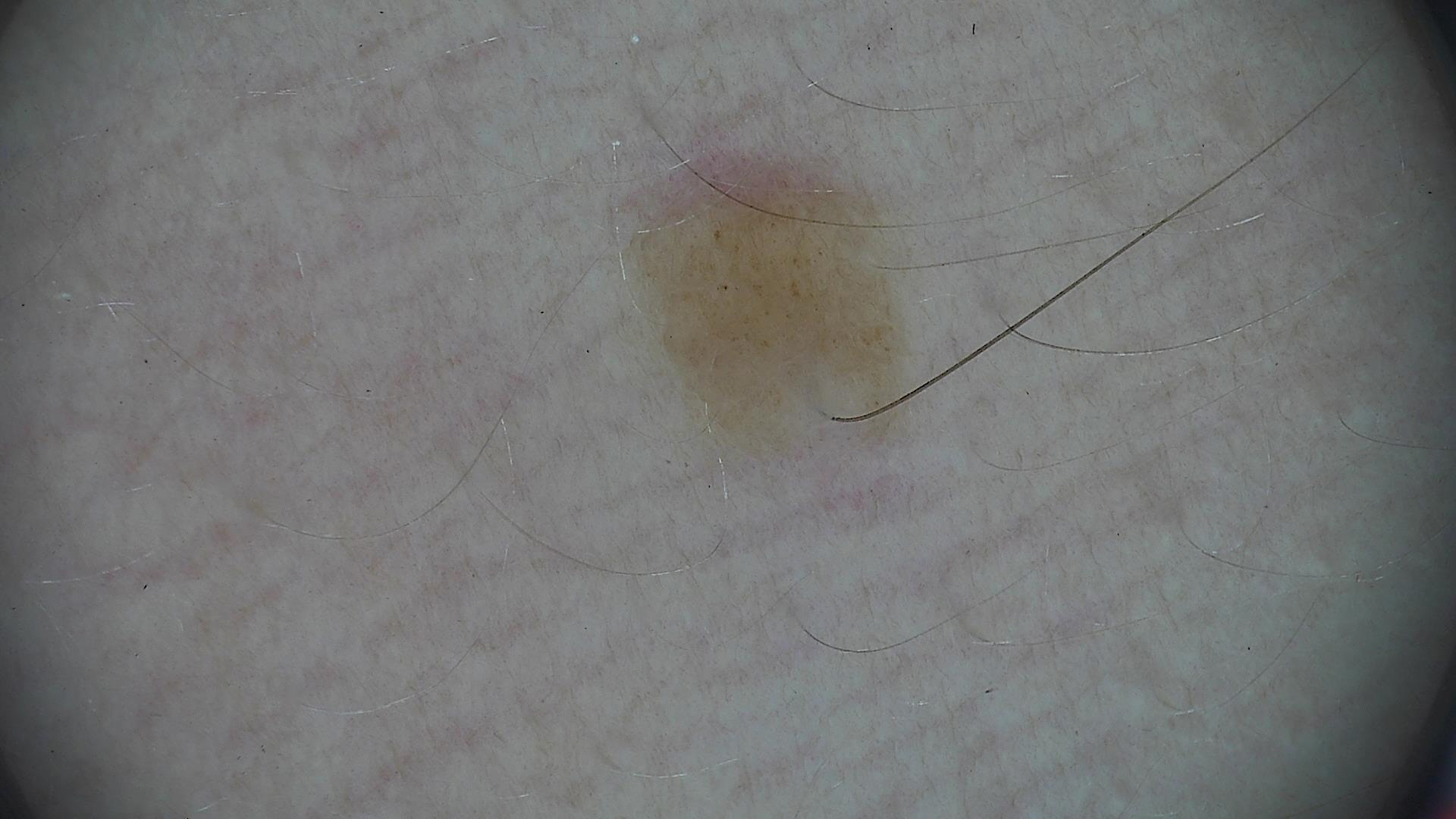Labeled as a dysplastic junctional nevus.